The contributor notes the condition has been present for about one day, the contributor notes the lesion is raised or bumpy, the lesion is associated with enlargement, the subject is a female aged 40–49, this is a close-up image, located on the head or neck, skin tone: Fitzpatrick III; human graders estimated a Monk Skin Tone of 2.
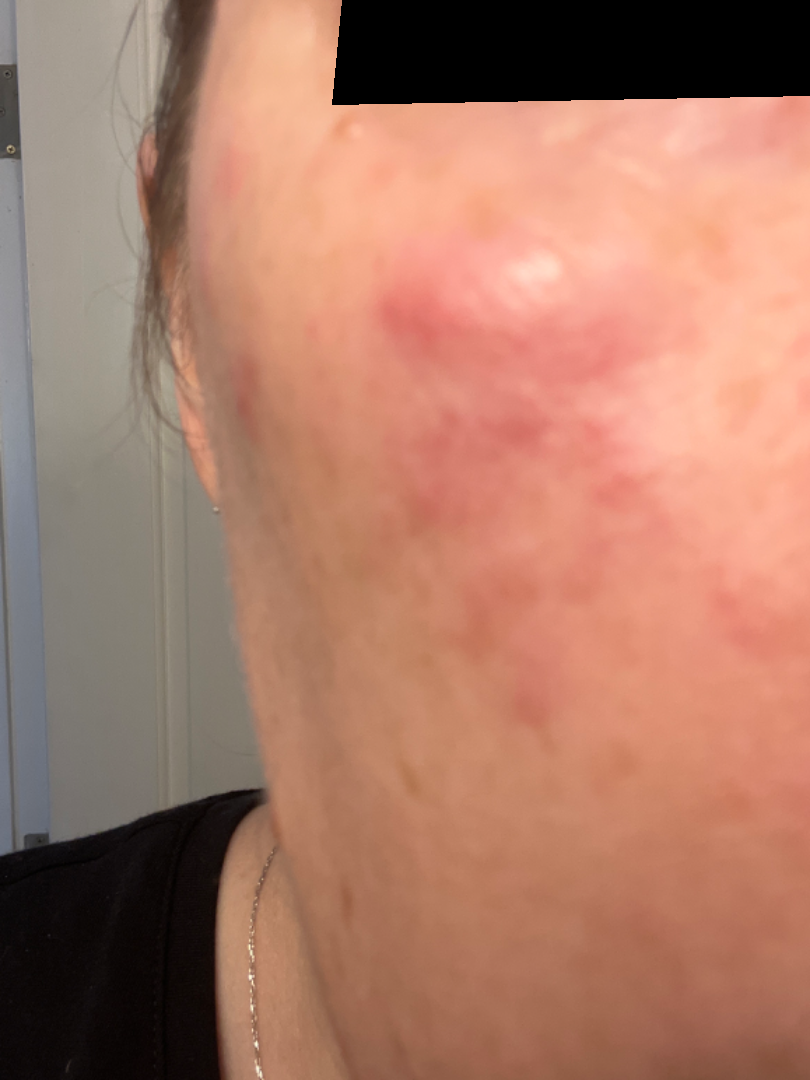Q: What is the dermatologist's impression?
A: the leading impression is Acne; the differential also includes Rosacea